The lesion involves the arm · an image taken at an angle · the subject is 30–39, male.
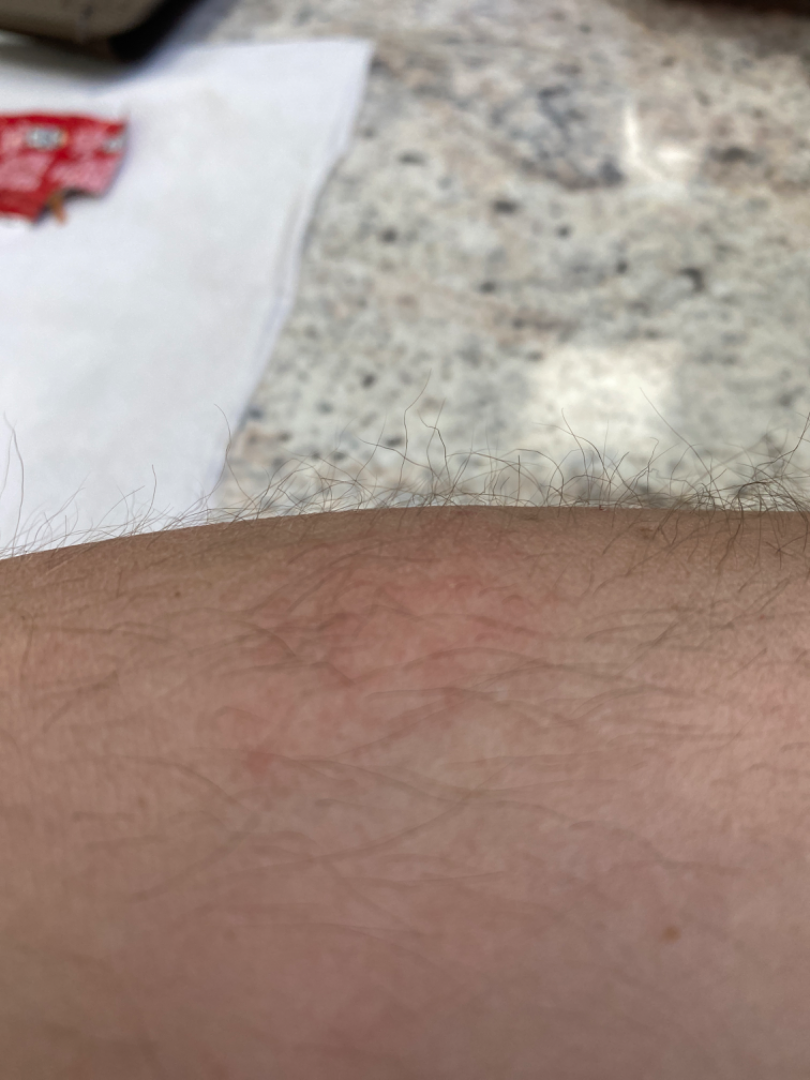{
  "assessment": "ungradable on photographic review",
  "systemic_symptoms": "none reported",
  "duration": "about one day",
  "texture": "raised or bumpy",
  "patient_category": "a rash",
  "symptoms": "itching"
}